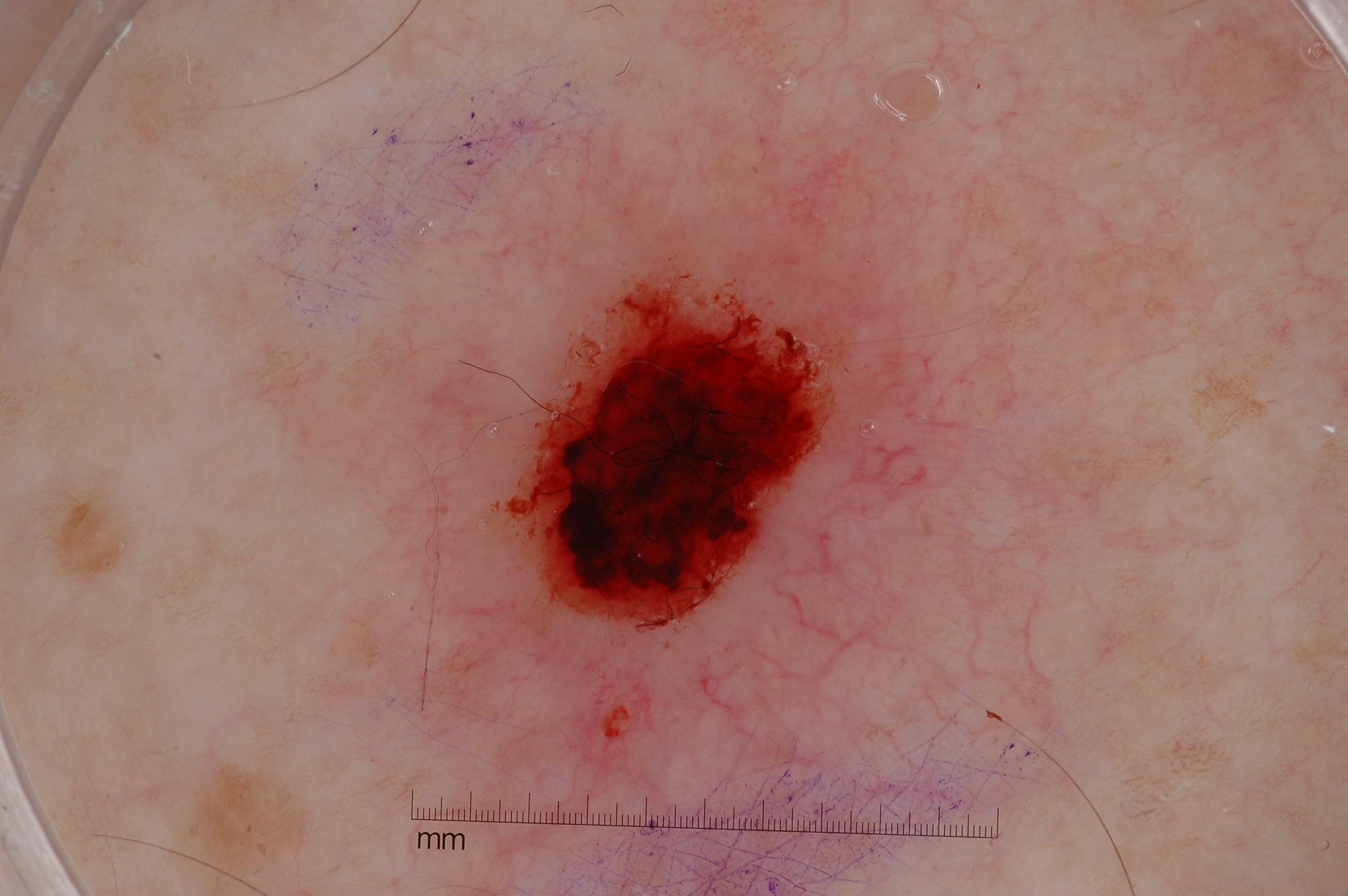subject: male, about 45 years old; imaging: dermoscopy of a skin lesion; dermoscopic features not present: negative network, milia-like cysts, pigment network, and streaks; size: moderate; lesion bbox: <box>495, 238, 895, 637</box>; diagnostic label: a seborrheic keratosis, a benign lesion.